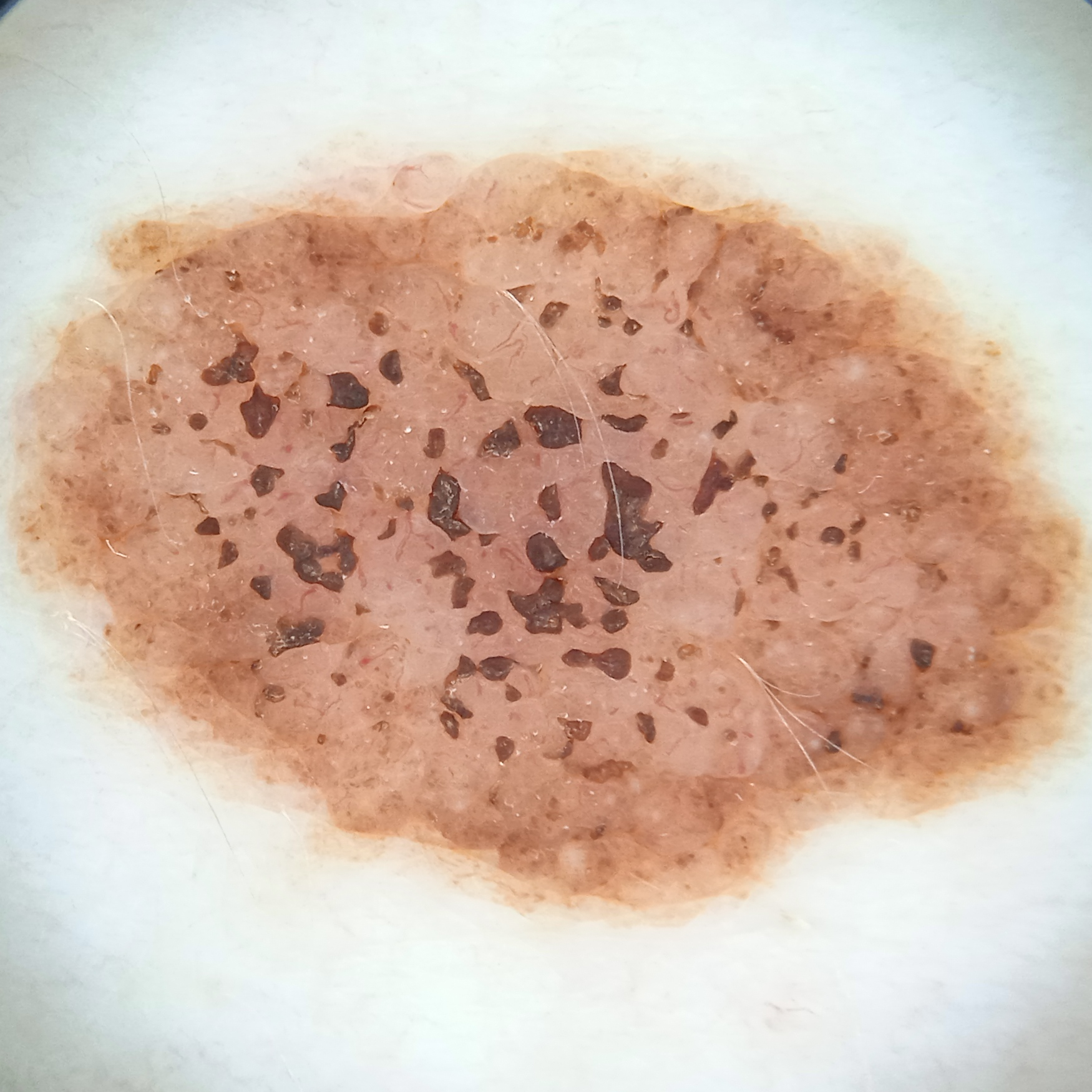Case:
– referral — research study (no referral diagnosis)
– sun reaction — skin reddens with sun exposure
– nevus count — numerous melanocytic nevi
– modality — dermoscopy
– patient — female, aged 26
– risk factors — a history of sunbed use
– location — the torso
– diameter — 12.1 mm
– diagnosis — melanocytic nevus (dermatologist consensus)